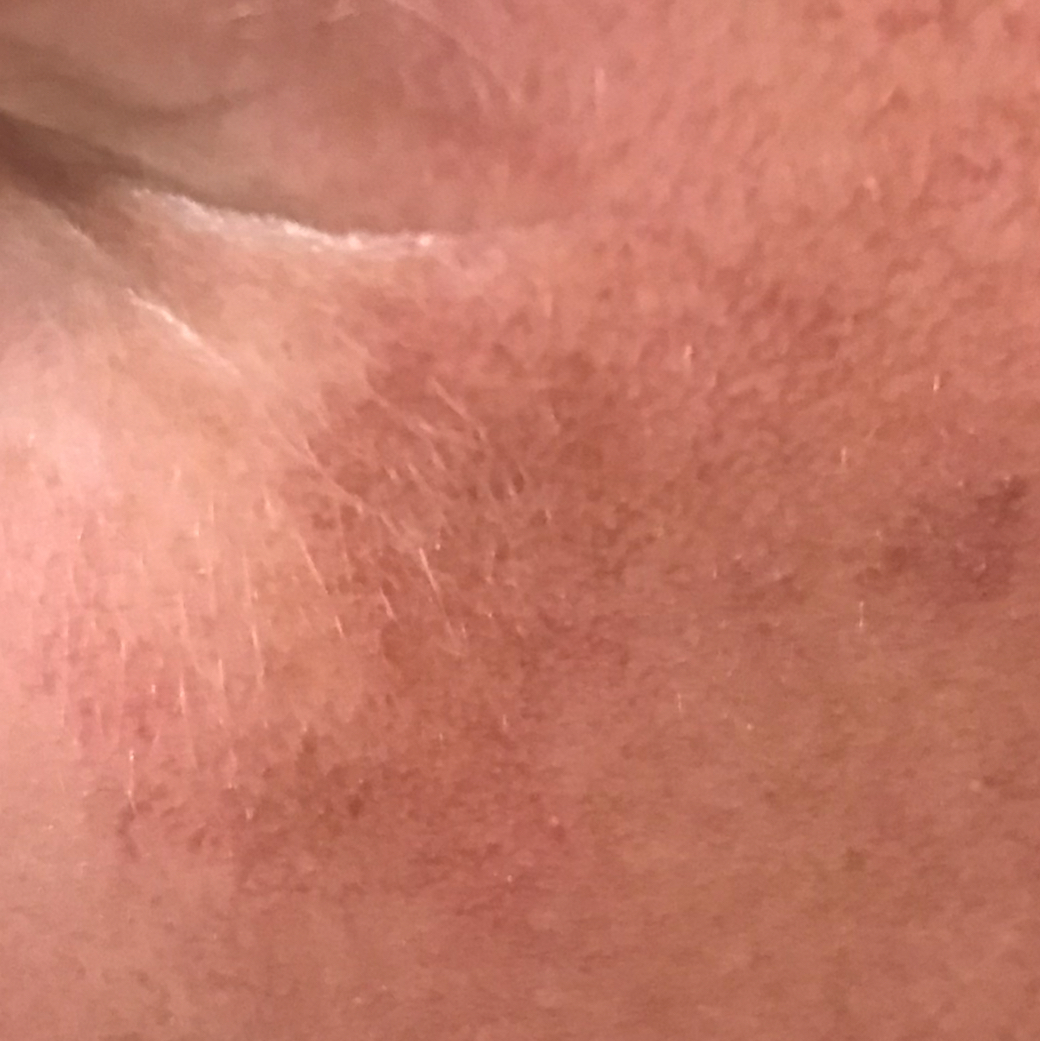Conclusion: Expert review favored an actinic keratosis.